A dermoscopic image of a skin lesion: 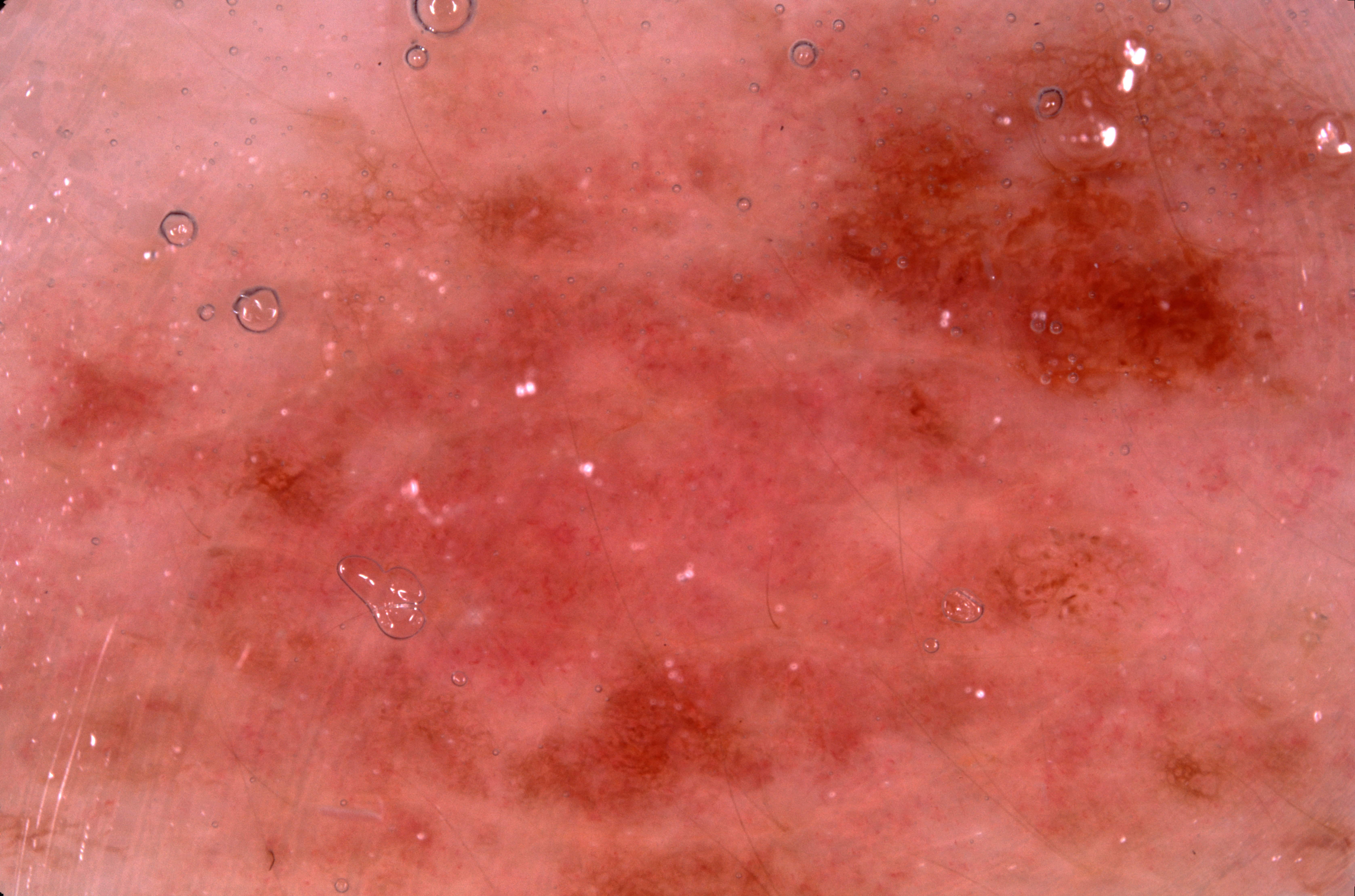Case summary:
- dermoscopic features · pigment network; absent: milia-like cysts, streaks, and negative network
- lesion location · spans the dermoscopic field
- assessment · a melanocytic nevus